A dermoscopic view of a skin lesion; a female subject, in their mid- to late 40s: 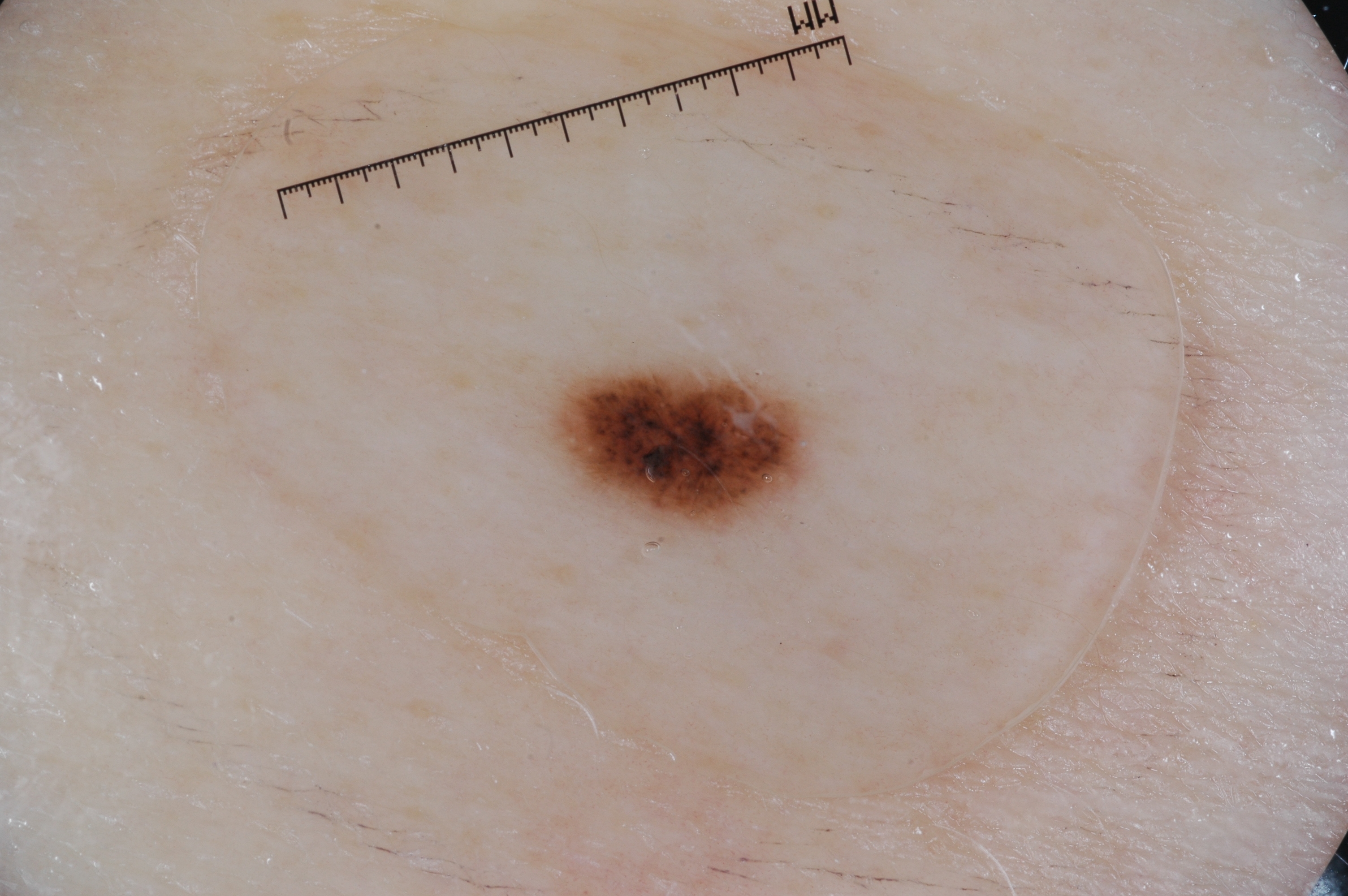Q: Which assessed dermoscopic features were absent?
A: milia-like cysts, pigment network, streaks, and negative network
Q: How much of the field does the lesion occupy?
A: ~3% of the field
Q: Where is the lesion located?
A: bbox=[548, 364, 822, 532]
Q: What is the diagnosis?
A: a melanocytic nevus, a benign lesion